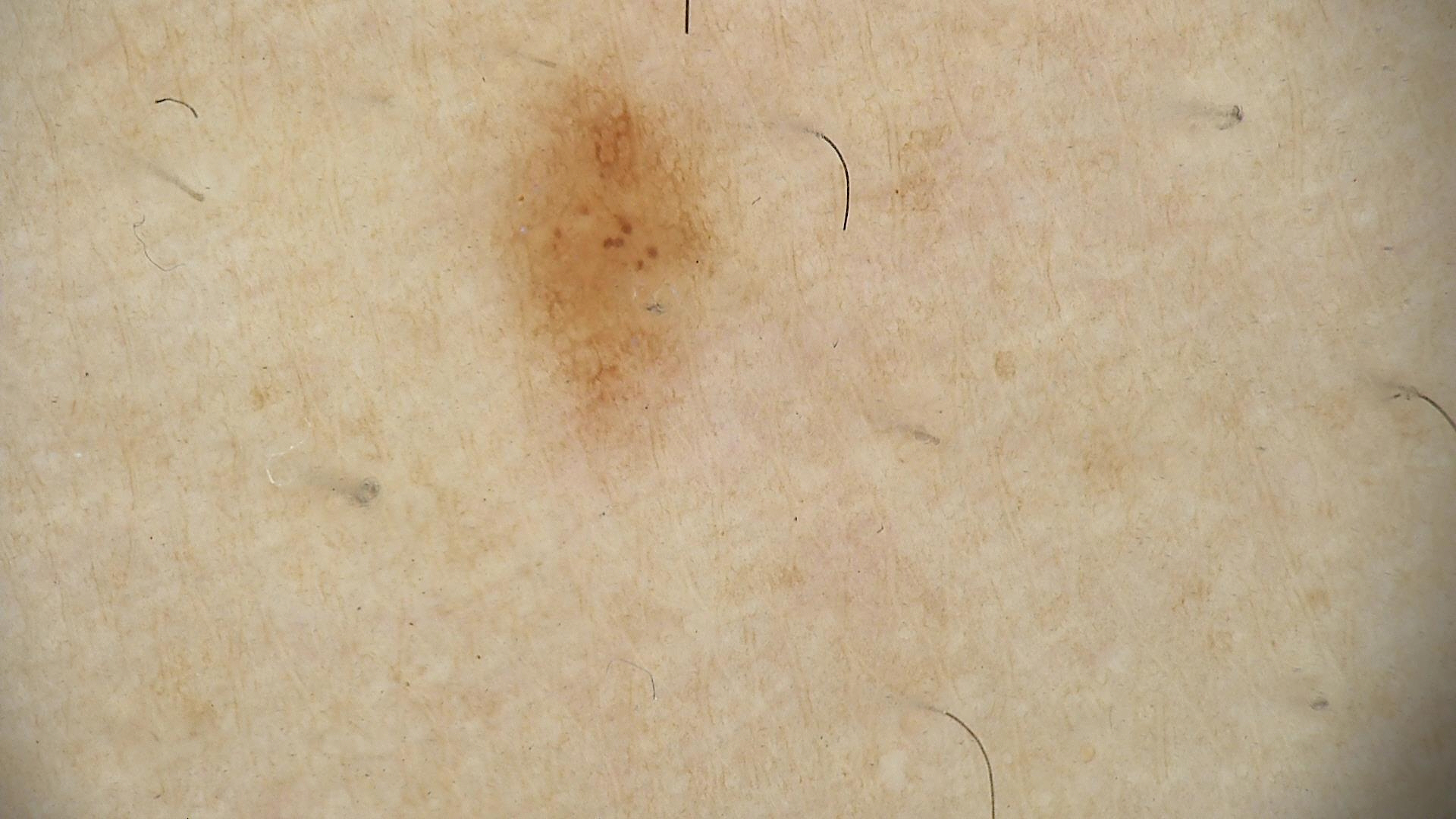The diagnostic label was a dysplastic junctional nevus.